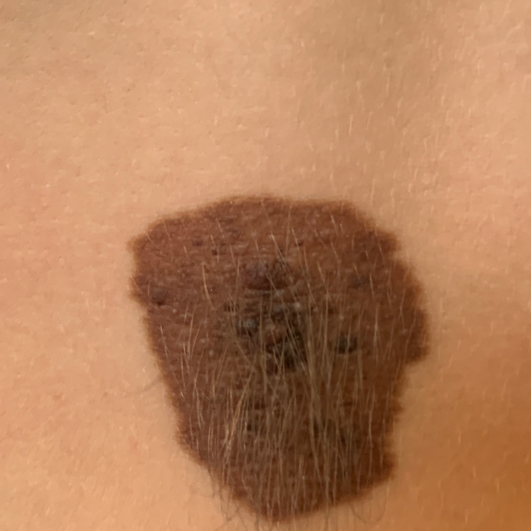modality: clinical photograph; patient: age 6; location: the back; patient-reported symptoms: growth, elevation / no bleeding; assessment: nevus (clinical consensus).